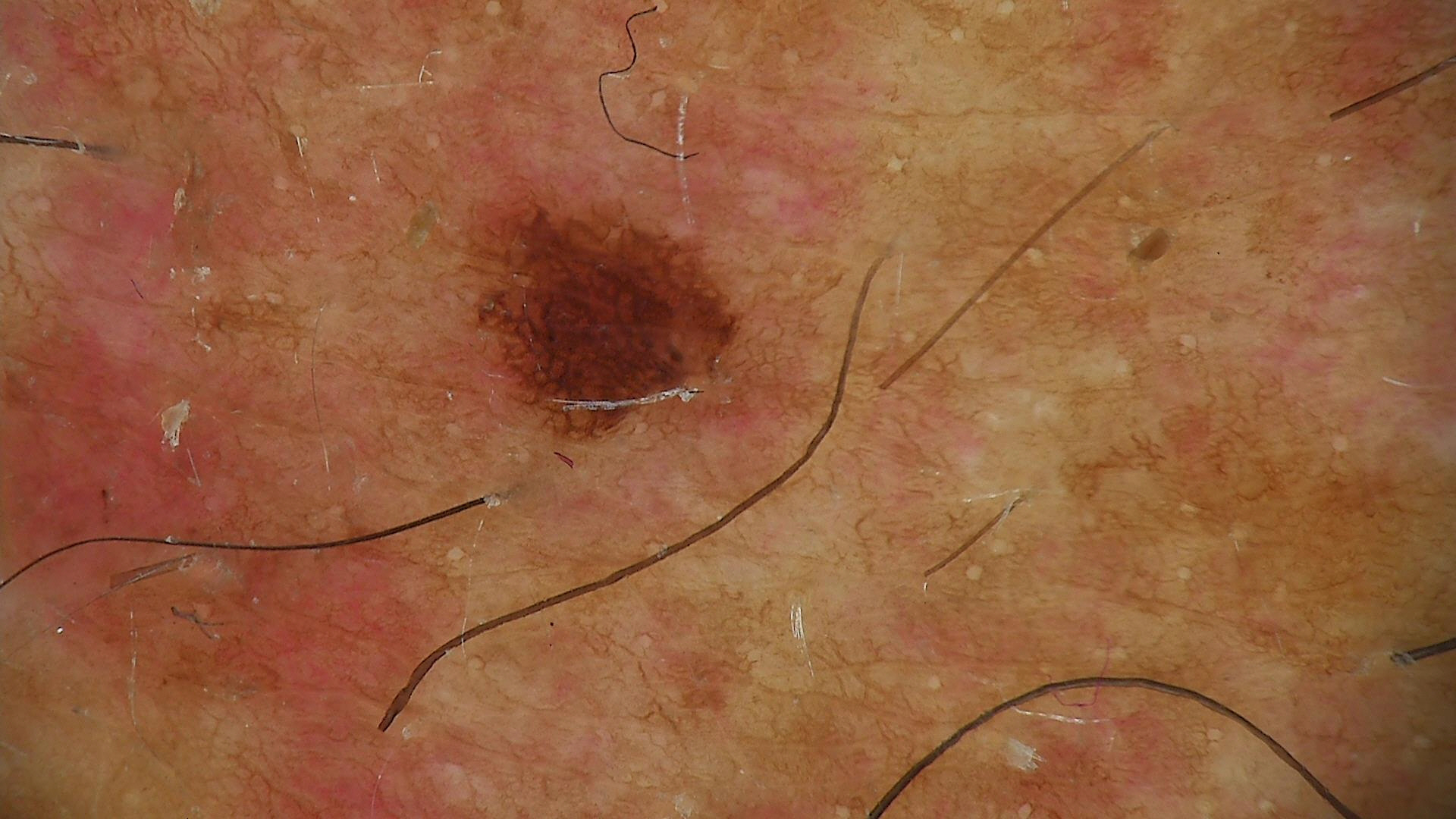Impression: The diagnostic label was a dysplastic junctional nevus.